A skin lesion imaged with a dermatoscope:
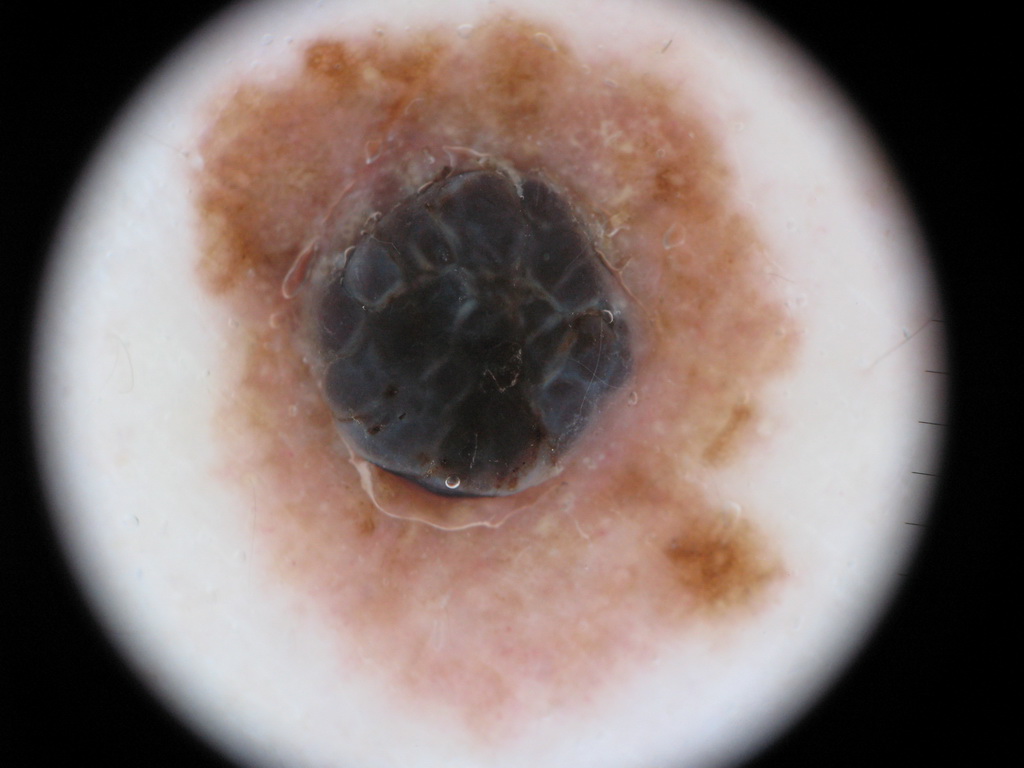Findings:
• dermoscopic pattern — pigment network
• bounding box — x1=187, y1=5, x2=799, y2=731
• diagnostic label — a melanoma, a malignant lesion